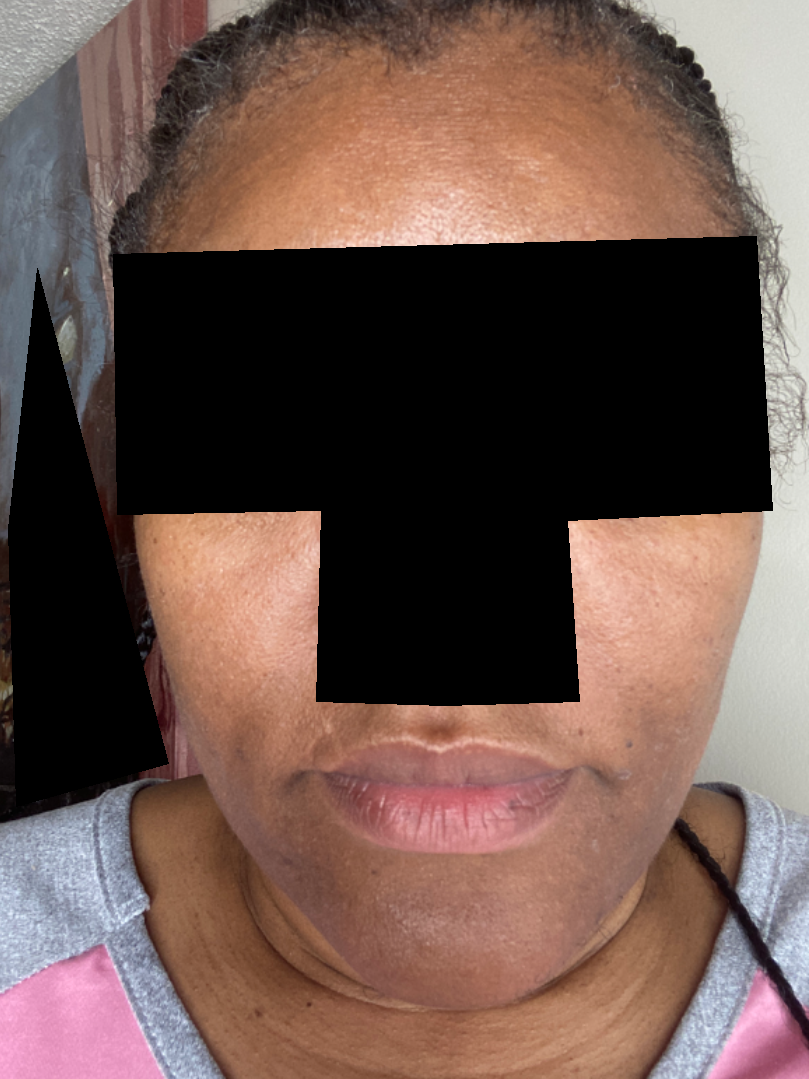Impression: No skin condition was discernible on photographic review. History: This is a close-up image. Texture is reported as rough or flaky. Symptoms reported: itching.